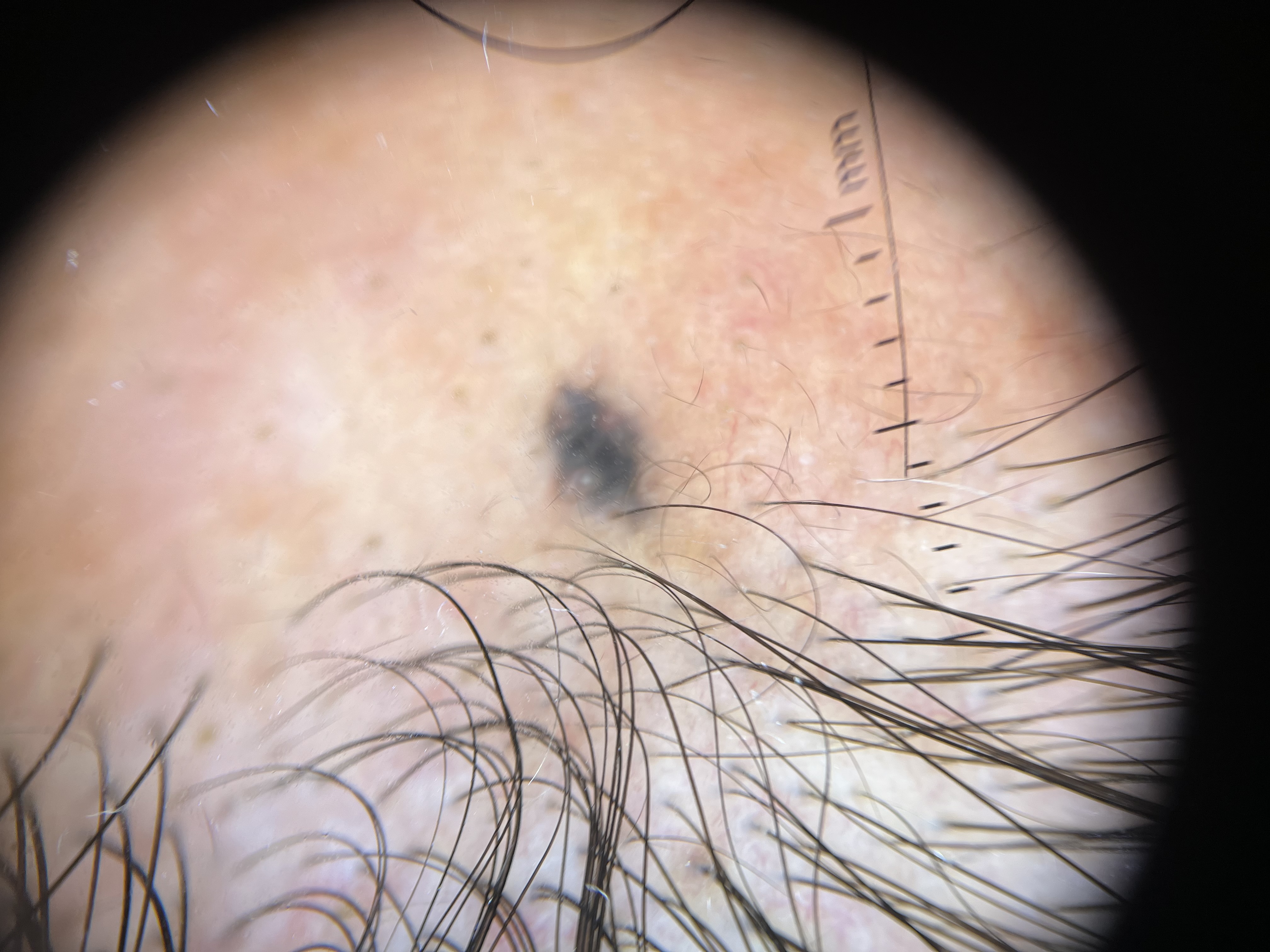The diagnostic label was a dermal lesion — a blue nevus.